A smartphone photograph of a skin lesion — 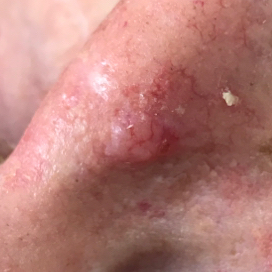Located on the nose.
The patient reports that the lesion itches and is elevated, but does not hurt and has not bled.
The biopsy diagnosis was a basal cell carcinoma.